The photo was captured at an angle; the lesion involves the arm: 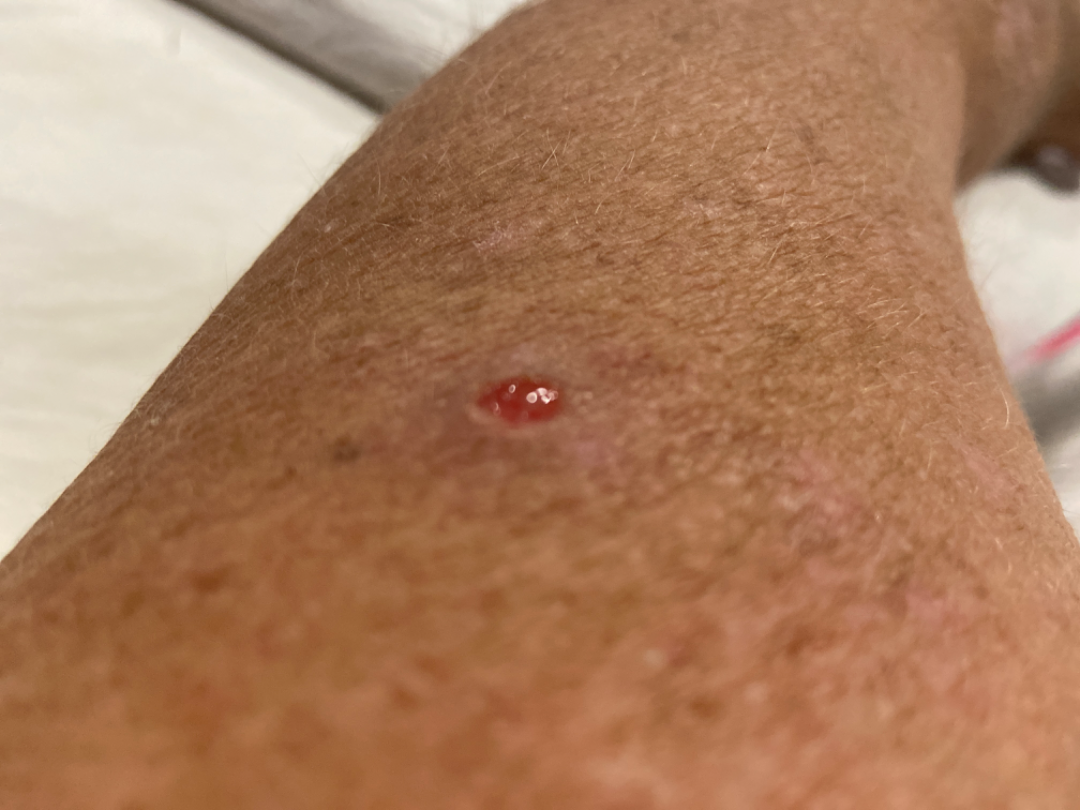Notes:
• assessment · ungradable on photographic review